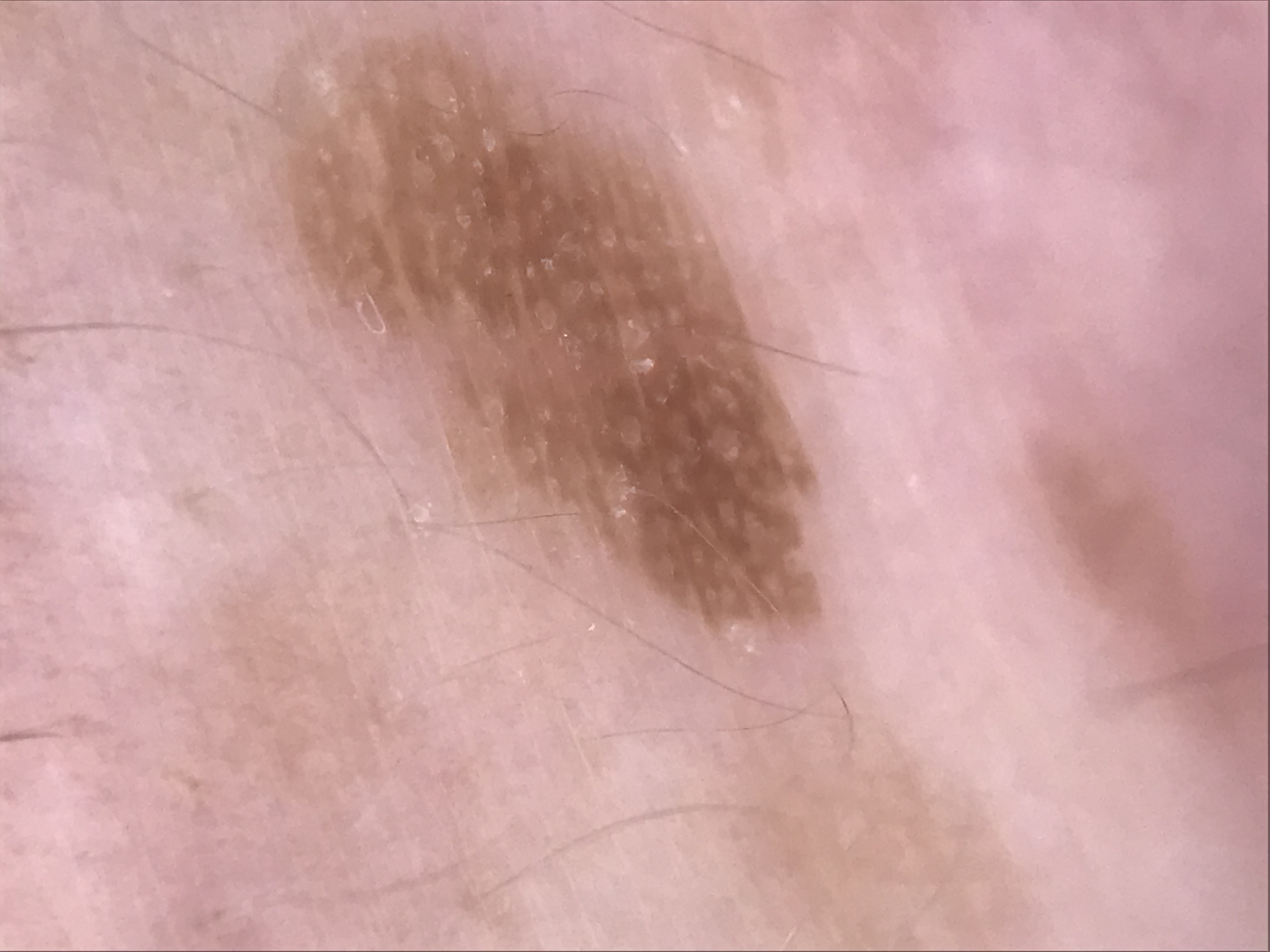Case:
A dermoscopic photograph of a skin lesion. The architecture is that of a keratinocytic lesion.
Conclusion:
The diagnosis was a benign lesion — a seborrheic keratosis.